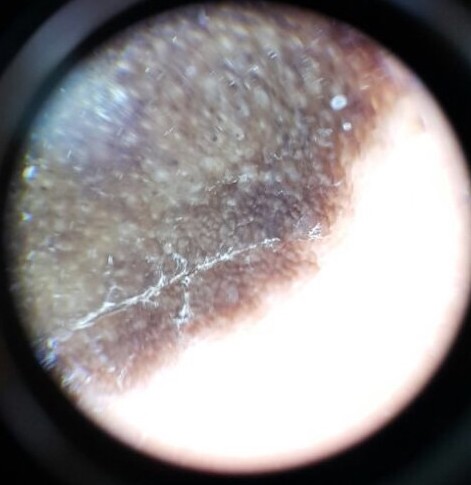modality: dermatoscopy; lesion type: banal; assessment: congenital compound nevus (expert consensus).